The patient describes having a moderate number of moles · the patient says their skin tans without first burning · a dermoscopy image of a skin lesion · a male subject aged 72 · collected as part of a research study, without a referral diagnosis: 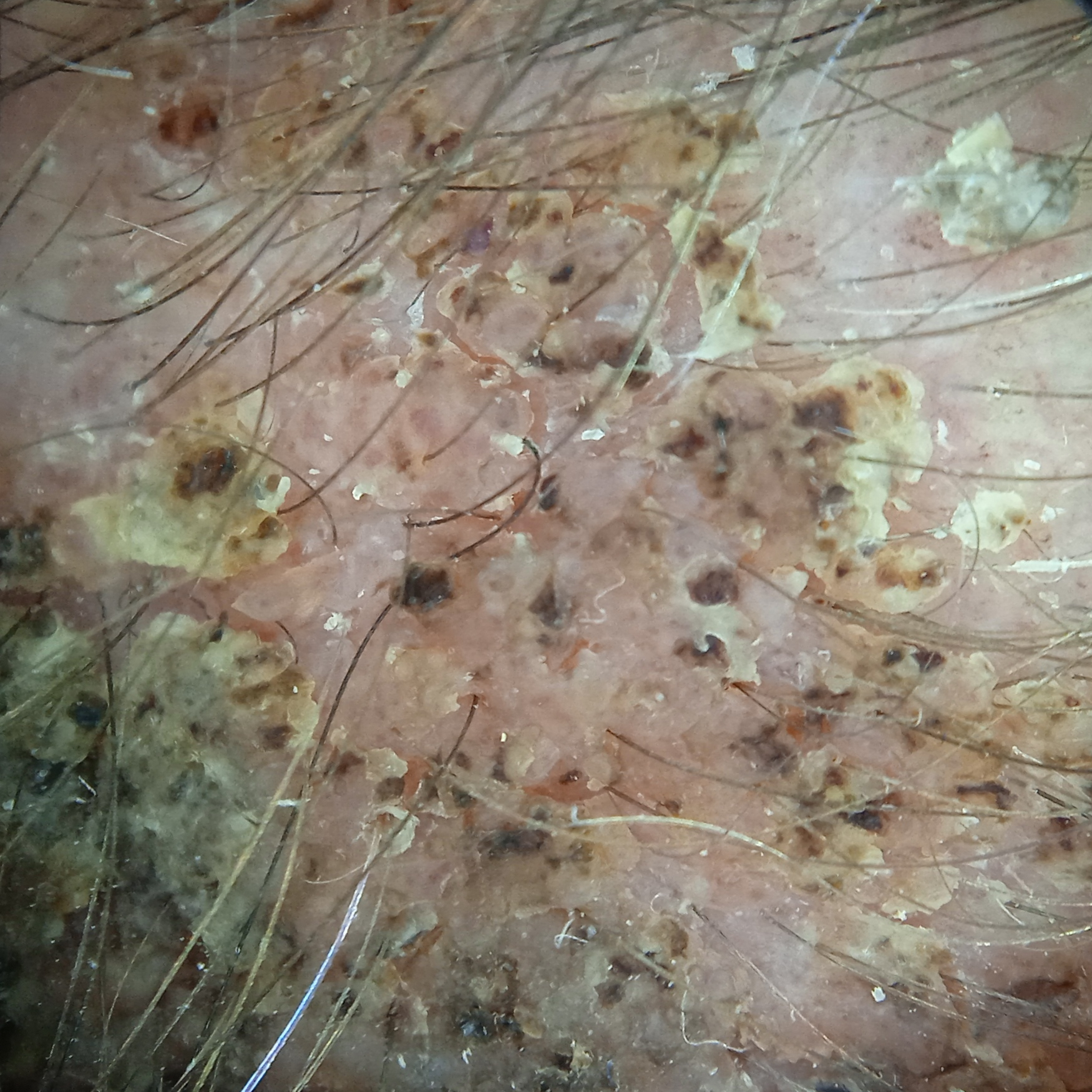Located on the head. Measuring roughly 19.2 mm. The diagnostic impression was a seborrheic keratosis.